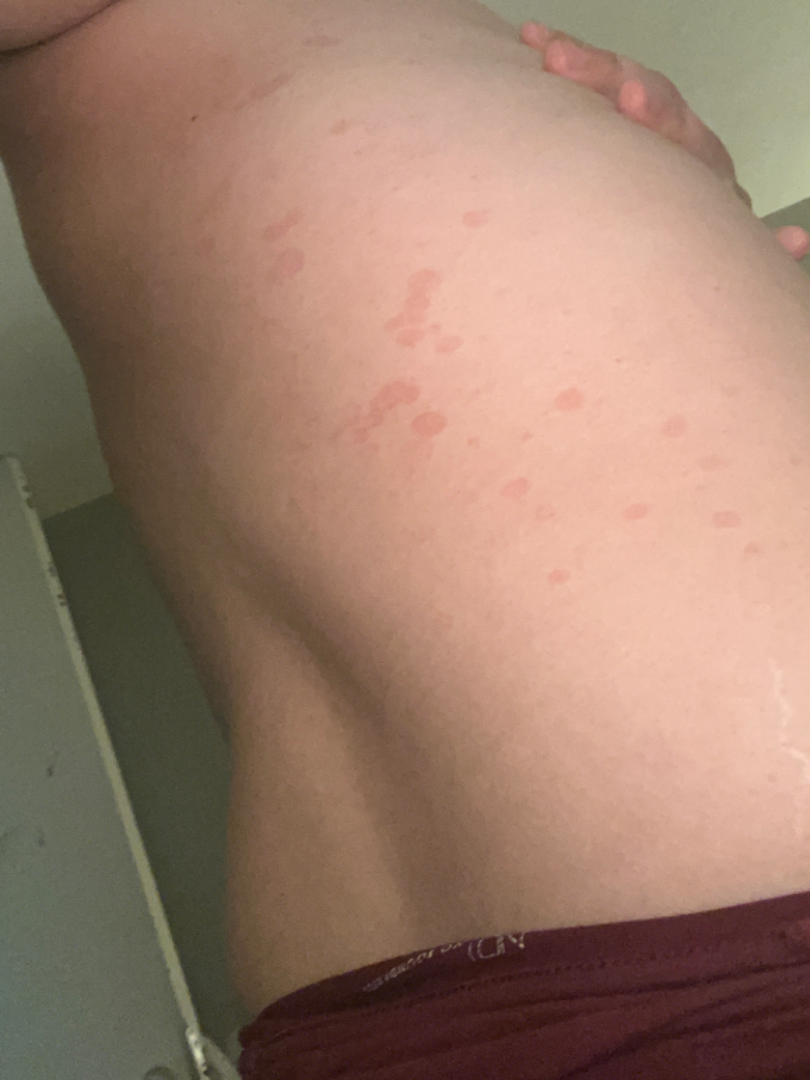Q: What conditions are considered?
A: reviewed remotely by one dermatologist: the differential, in no particular order, includes Tinea Versicolor and Seborrheic Dermatitis